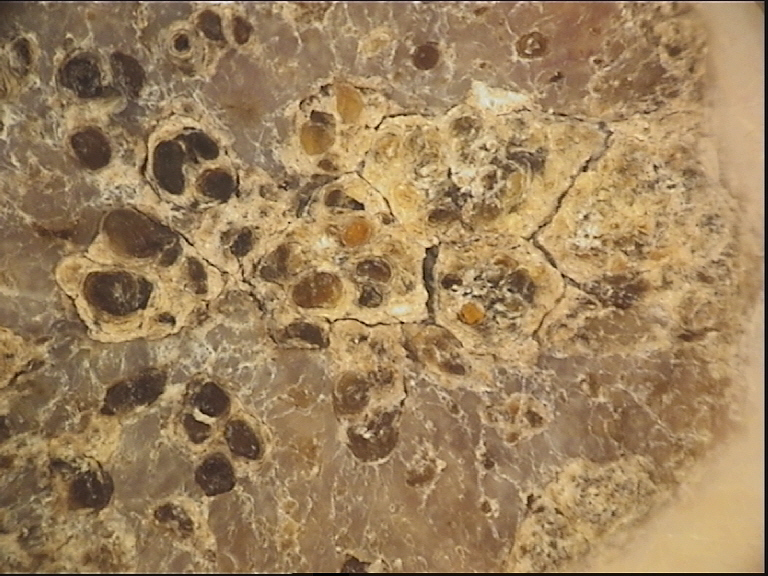Findings:
A dermoscopy image of a single skin lesion.
Impression:
The diagnosis was a seborrheic keratosis.